The lesion involves the arm, this image was taken at an angle: 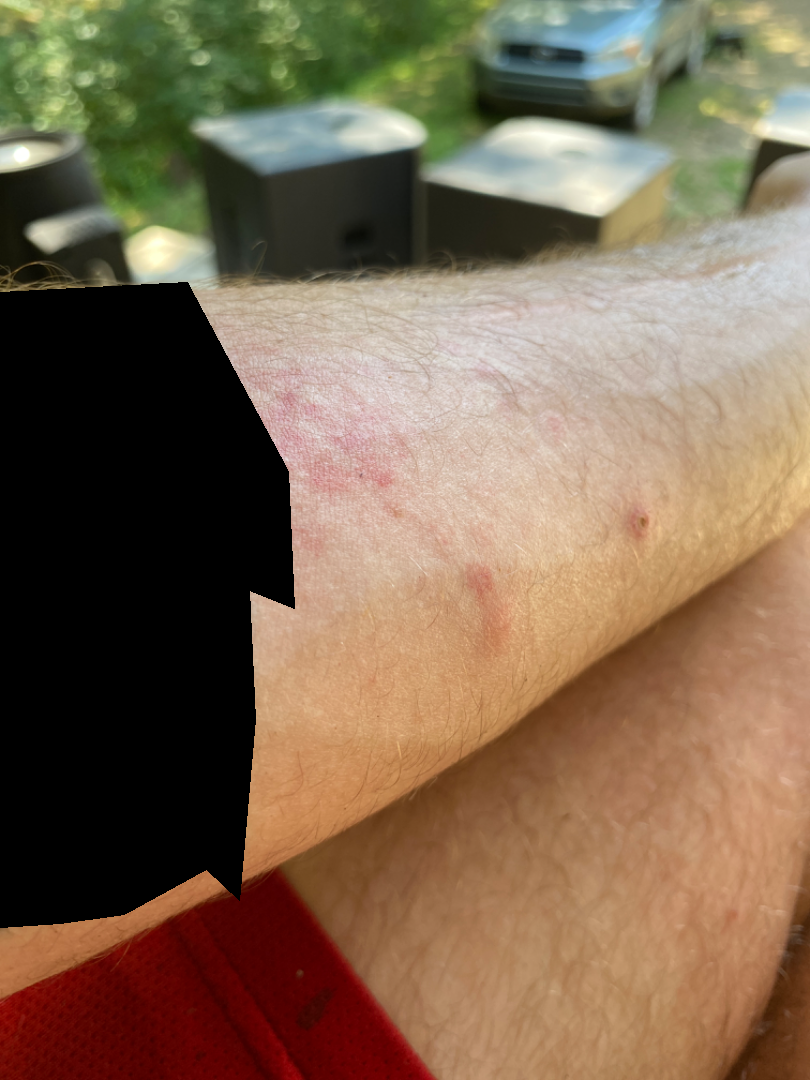<report>
<assessment>unable to determine</assessment>
<texture>flat</texture>
<duration>about one day</duration>
<skin_tone>
  <fitzpatrick>III</fitzpatrick>
  <monk_skin_tone>2</monk_skin_tone>
</skin_tone>
</report>